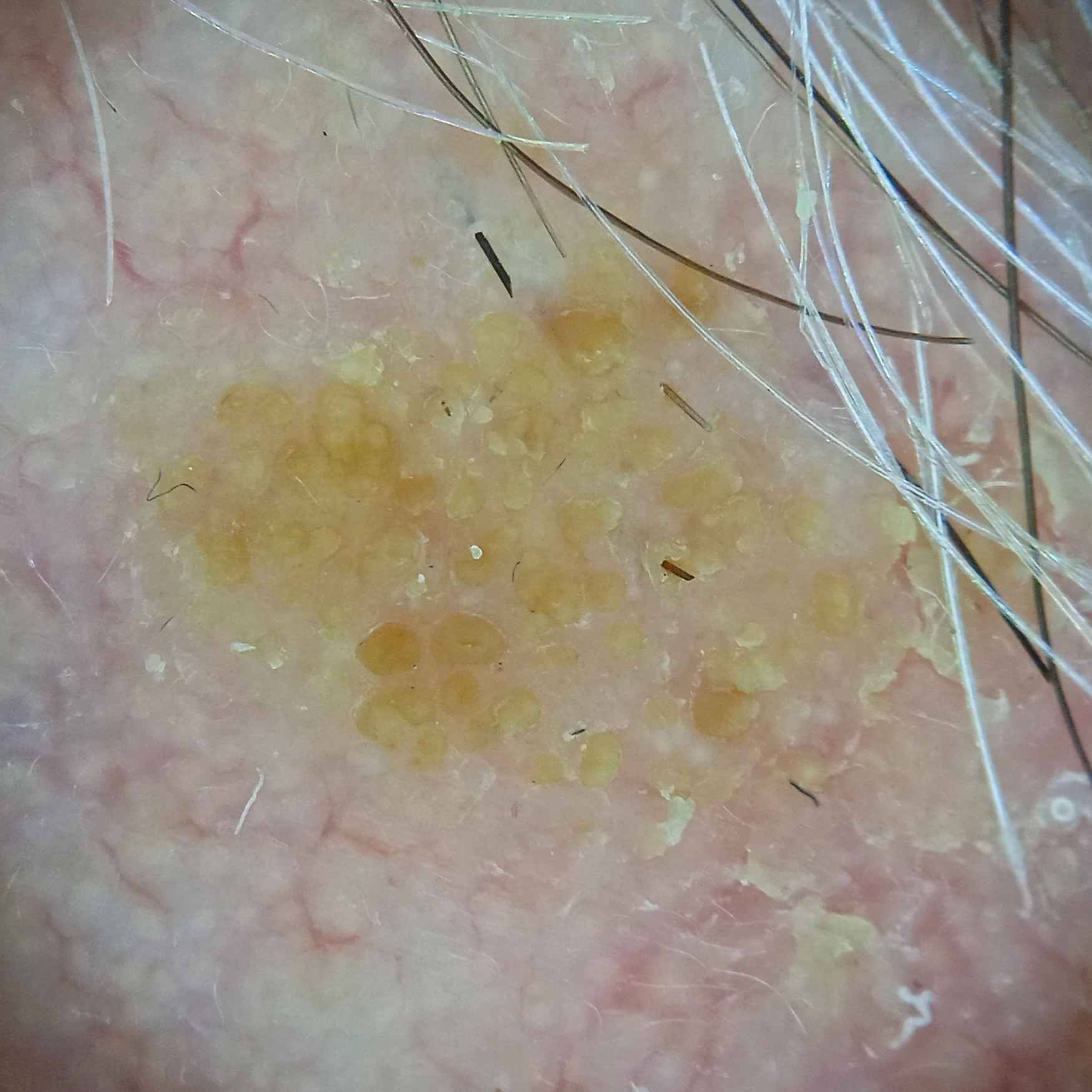Conclusion: Dermatologist review favored a seborrheic keratosis.